A dermoscopic close-up of a skin lesion: 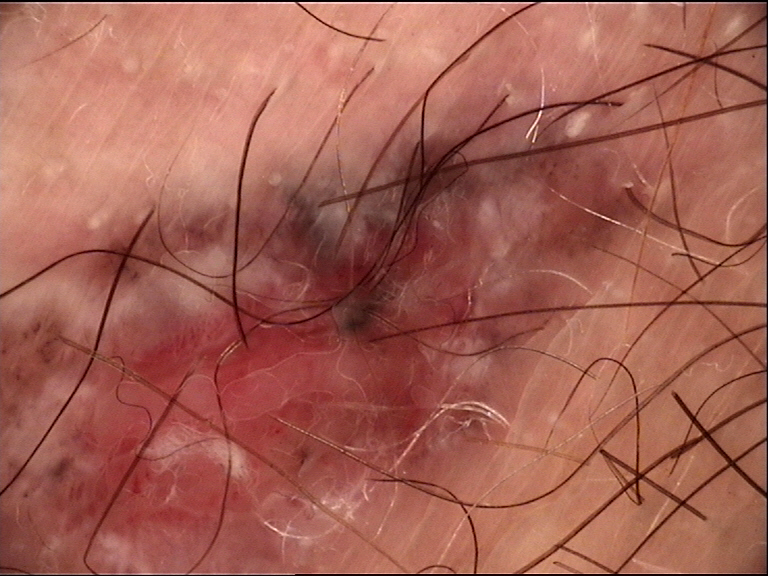Findings:
The architecture is that of a keratinocytic lesion.
Conclusion:
Histopathologically confirmed as a basal cell carcinoma.